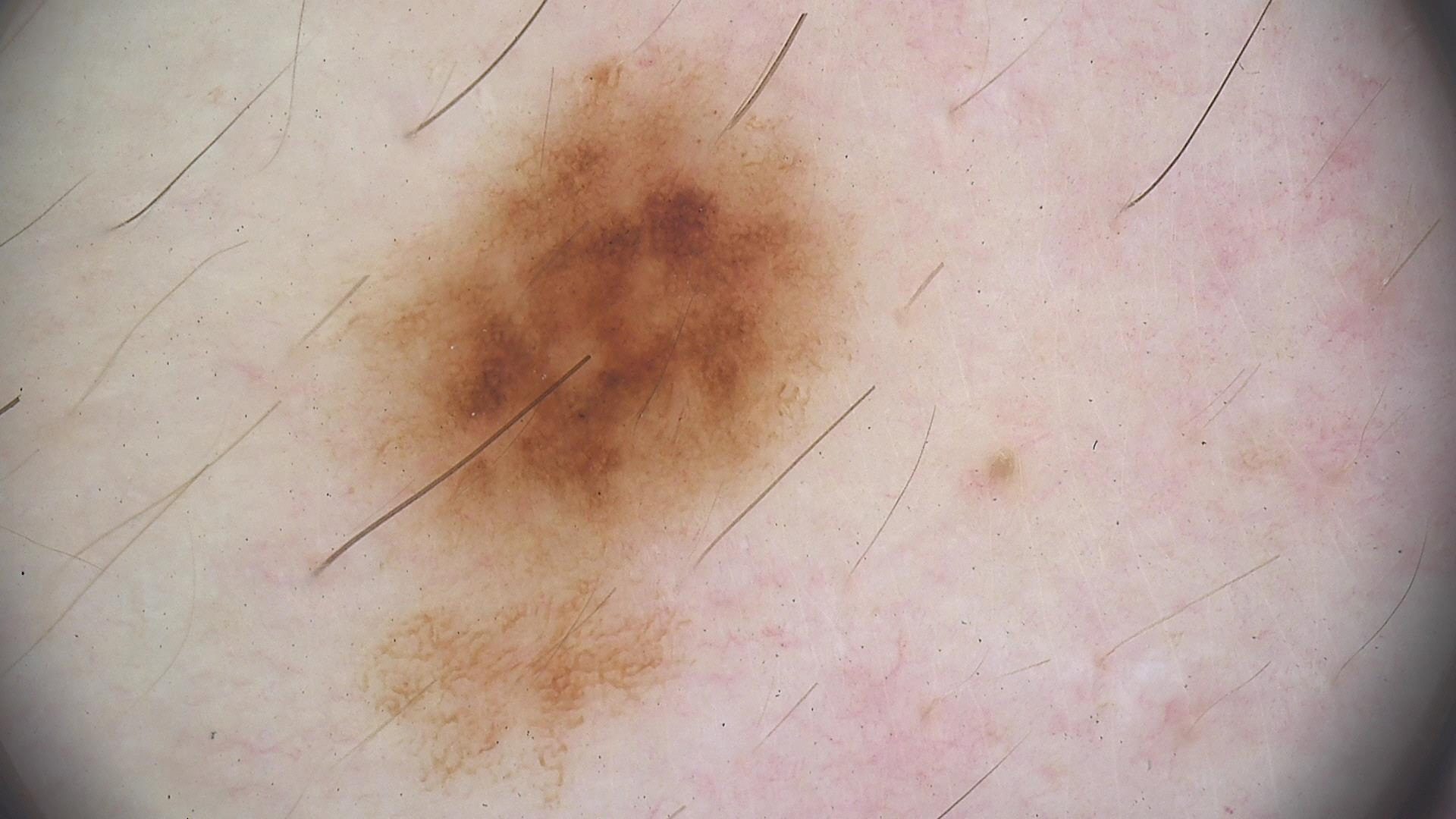  image: dermatoscopy
  diagnosis:
    name: dysplastic junctional nevus
    code: jd
    malignancy: benign
    super_class: melanocytic
    confirmation: expert consensus